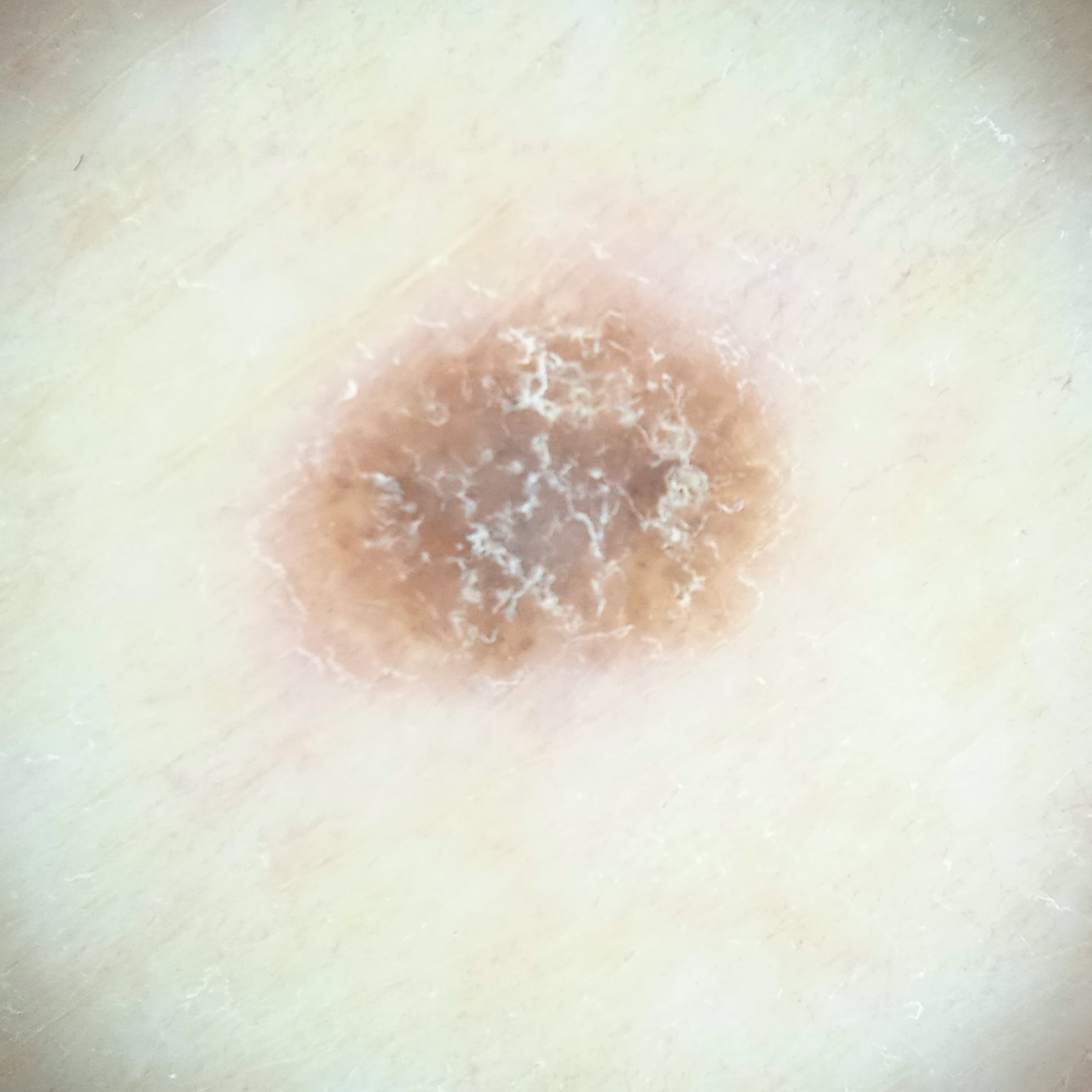{"mole_burden": "few melanocytic nevi overall", "patient": {"age": 79, "sex": "male"}, "image": "dermatoscopic image", "sun_reaction": "skin tans without first burning", "referral": "research study (no referral diagnosis)", "diagnosis": {"name": "seborrheic keratosis", "malignancy": "benign"}}